The contributor reports the lesion is raised or bumpy and rough or flaky · the patient considered this a rash · the photograph is a close-up of the affected area · reported duration is less than one week · FST III · the arm is involved · the contributor is 30–39, female · the contributor reports itching · the patient reported no systemic symptoms:
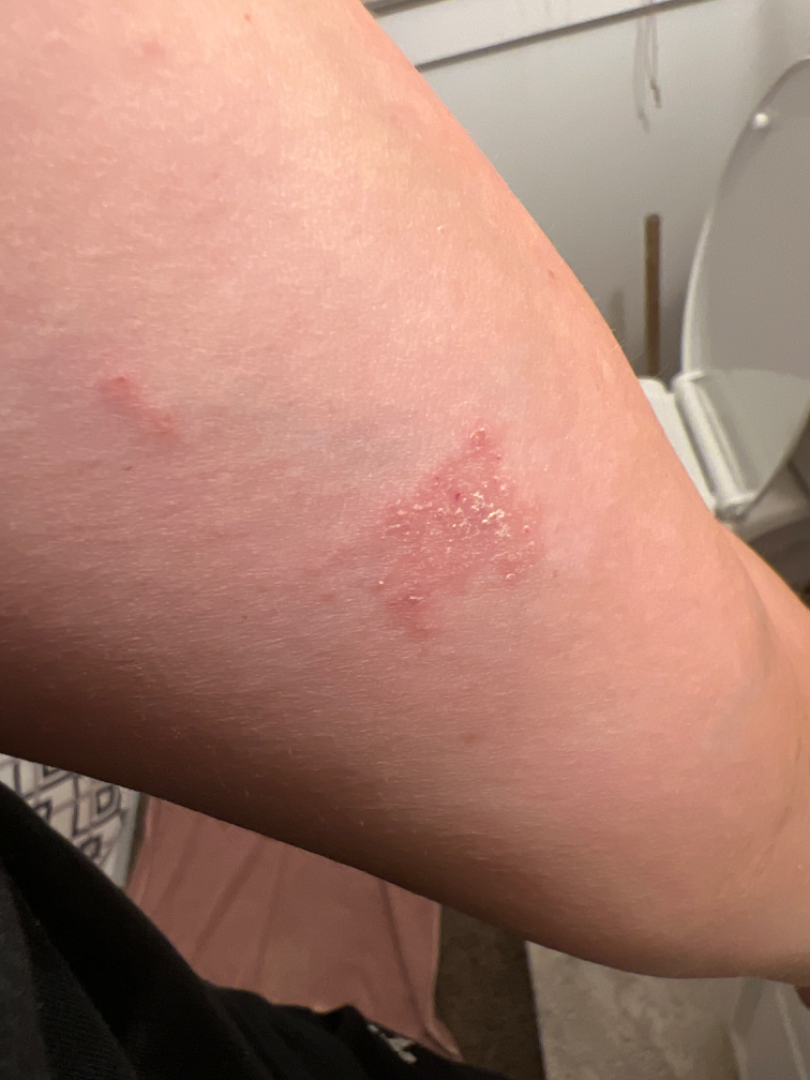{
  "differential": {
    "leading": [
      "Allergic Contact Dermatitis"
    ],
    "considered": [
      "Psoriasis"
    ],
    "unlikely": [
      "Eczema"
    ]
  }
}